By history, prior malignancy (patient or family), pesticide exposure, prior skin cancer (patient or family), and alcohol use. A clinical close-up photograph of a skin lesion. The patient is Fitzpatrick phototype I. A female patient in their late 50s:
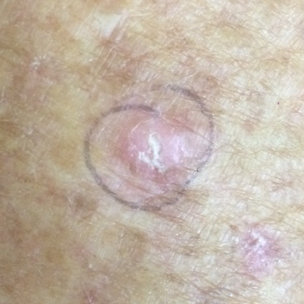body site: a forearm; diameter: 9x7 mm; symptoms: elevation, growth, itching / no change in appearance; pathology: squamous cell carcinoma (biopsy-proven).